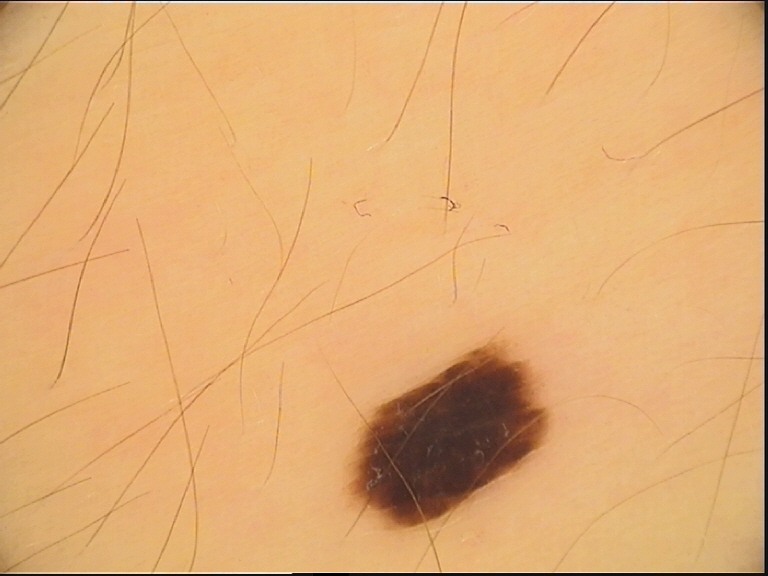The diagnostic label was a dysplastic junctional nevus.